A dermoscopic image of a skin lesion.
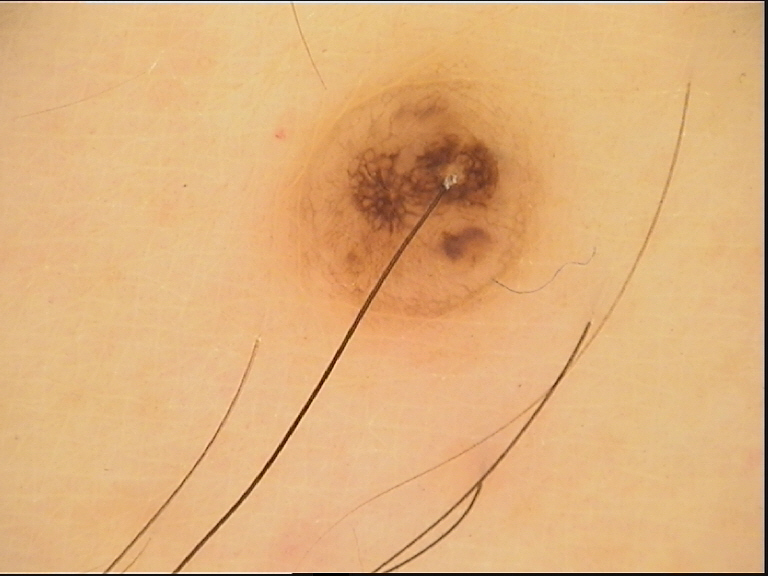  diagnosis:
    name: dermal nevus
    code: db
    malignancy: benign
    super_class: melanocytic
    confirmation: expert consensus